The affected area is the arm; the photo was captured at a distance; the contributor is female — 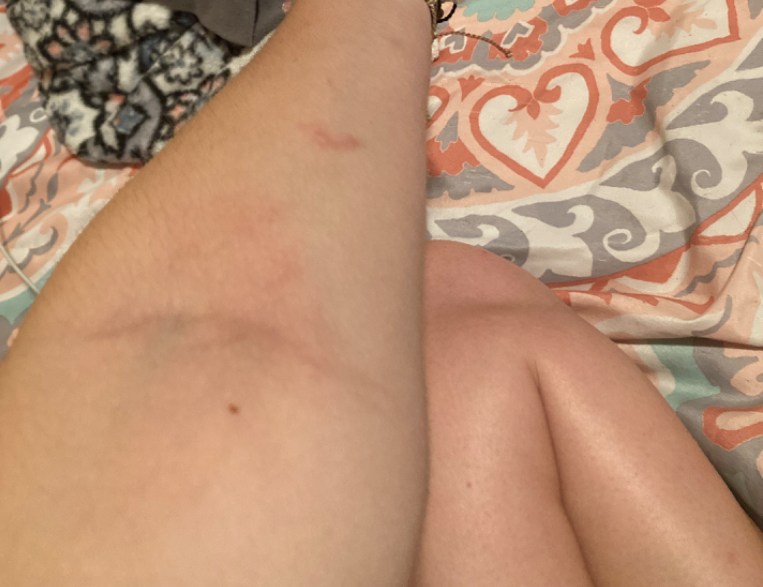Findings:
• texture · flat
• other reported symptoms · mouth sores and shortness of breath
• symptom duration · one to four weeks
• patient-reported symptoms · bothersome appearance and darkening
• diagnostic considerations · the leading impression is Contact dermatitis; an alternative is Pigmented purpuric eruption; possibly Morphea/Scleroderma; also on the differential is Post-Inflammatory hyperpigmentation